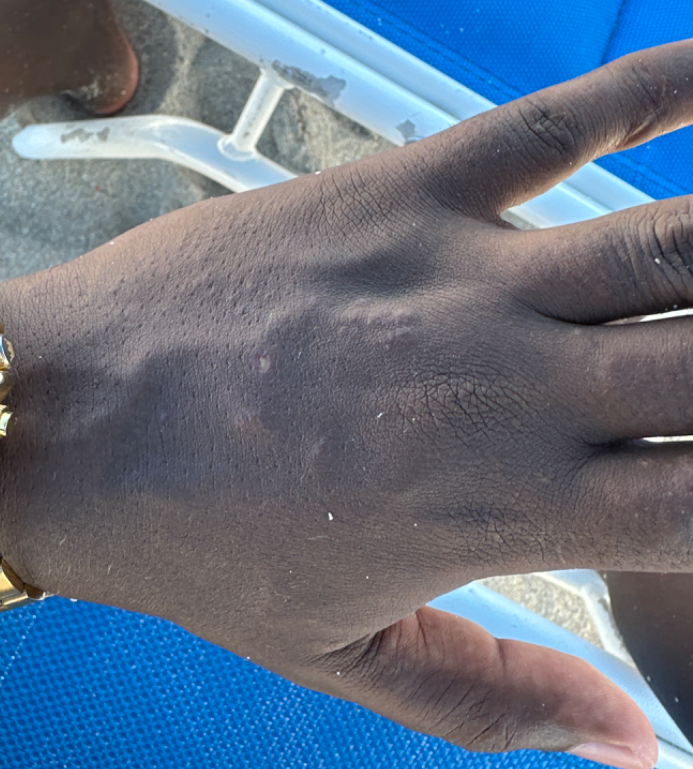Q: Could the case be diagnosed?
A: indeterminate from the photograph
Q: Where on the body?
A: arm, back of the hand and leg
Q: Fitzpatrick or Monk tone?
A: Fitzpatrick skin type V
Q: Texture?
A: fluid-filled, rough or flaky and raised or bumpy
Q: Patient's own categorization?
A: a rash
Q: Image view?
A: at a distance